The lesion is associated with itching · the photograph was taken at a distance · the patient is a female aged 30–39 · skin tone: FST III · texture is reported as raised or bumpy.
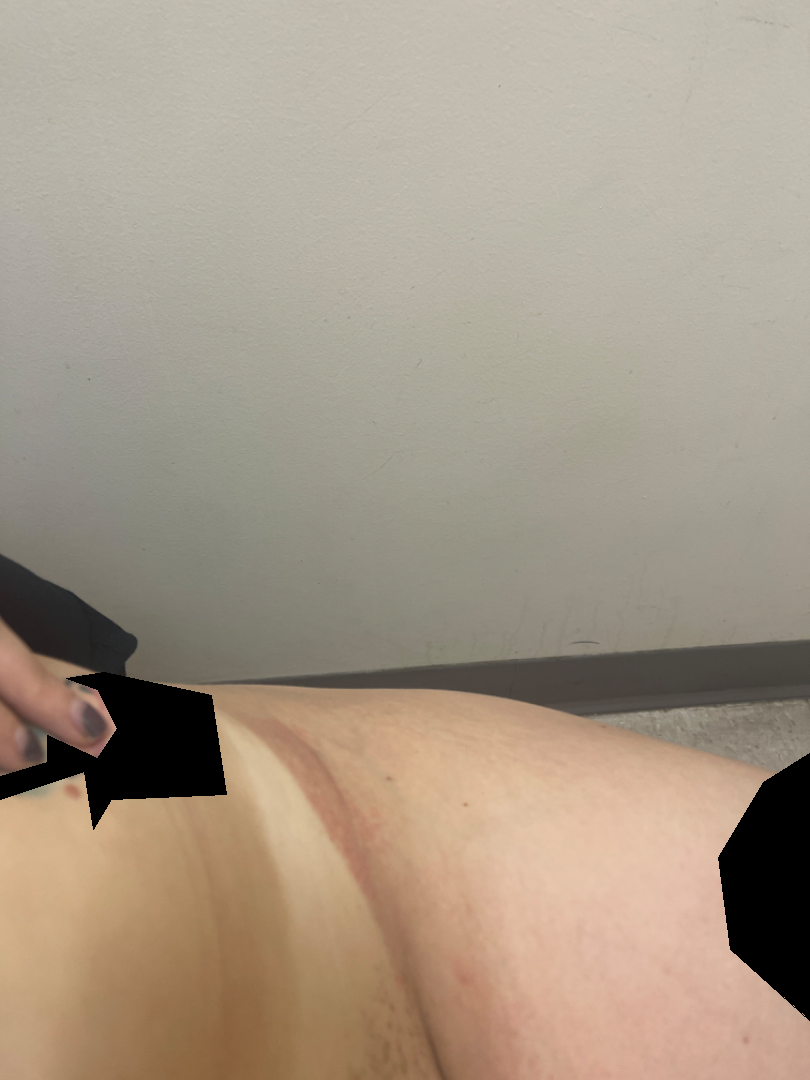clinical impression = Intertrigo and Allergic Contact Dermatitis were considered with similar weight; also consider Irritant Contact Dermatitis.